This image was taken at a distance · the lesion involves the arm — 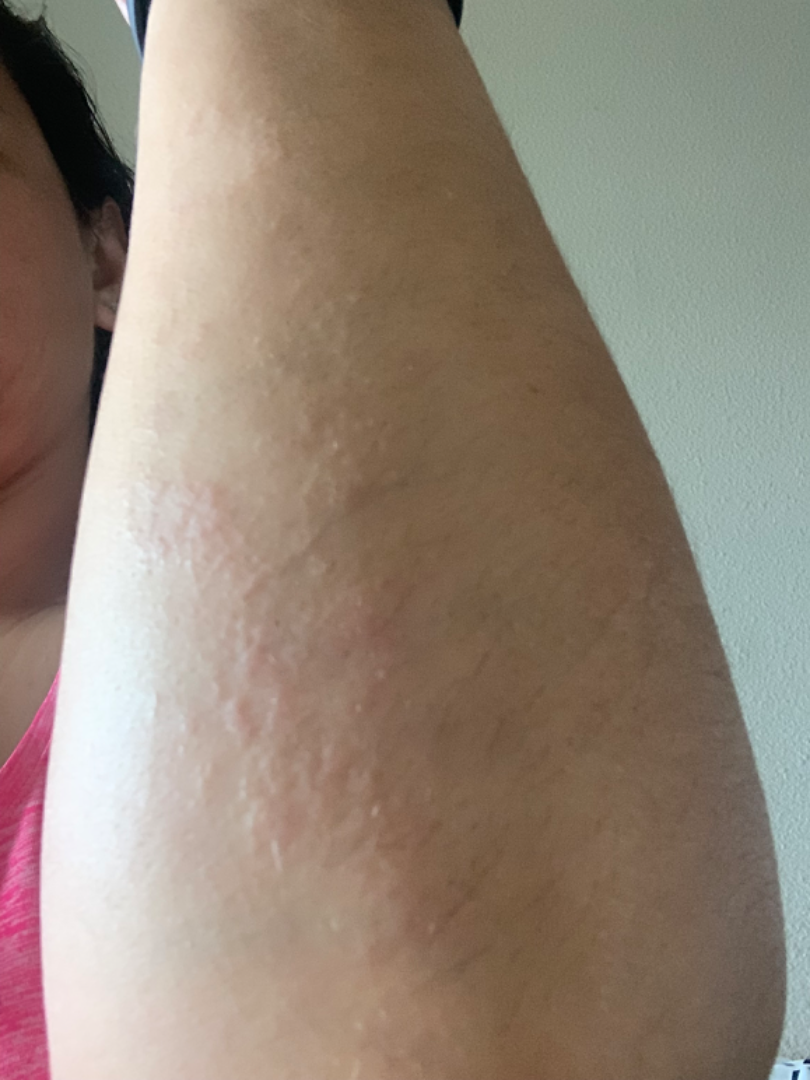{
  "duration": "one to four weeks",
  "texture": "raised or bumpy",
  "symptoms": "itching",
  "differential": {
    "tied_lead": [
      "Eczema",
      "Allergic Contact Dermatitis"
    ],
    "unlikely": [
      "Psoriasis"
    ]
  }
}